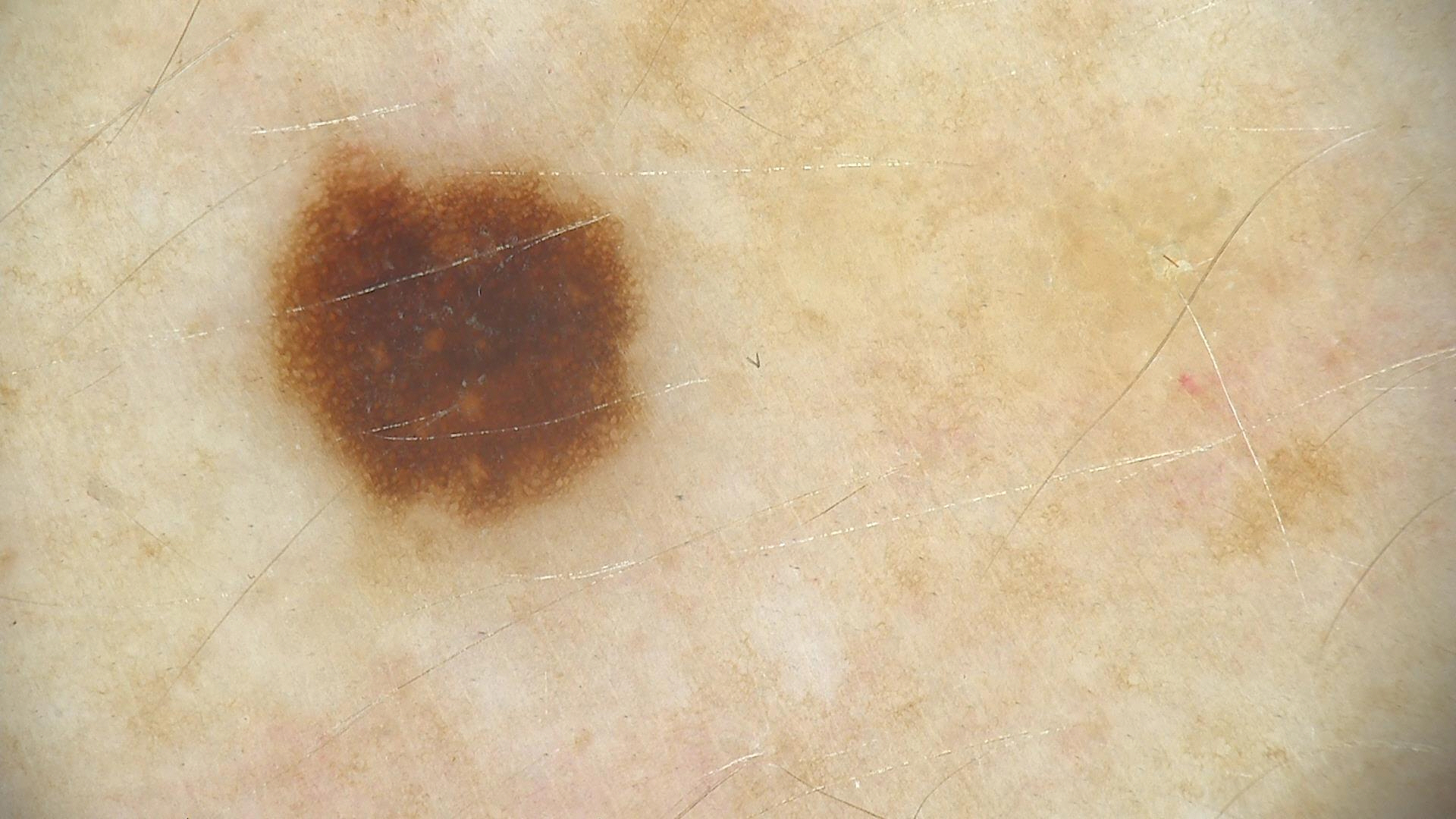Classified as a dysplastic junctional nevus.